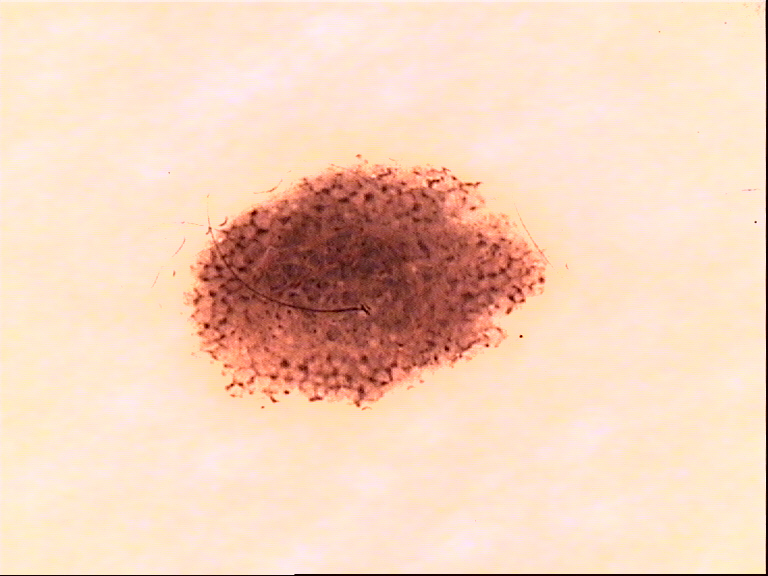{"image": "dermoscopy", "lesion_type": {"main_class": "banal", "pattern": "compound"}, "diagnosis": {"name": "compound nevus", "code": "cb", "malignancy": "benign", "super_class": "melanocytic", "confirmation": "expert consensus"}}